The subject is 18–29, female. No relevant systemic symptoms. The leg and arm are involved. Texture is reported as raised or bumpy. FST III; lay graders estimated 2 on the MST. This image was taken at an angle — 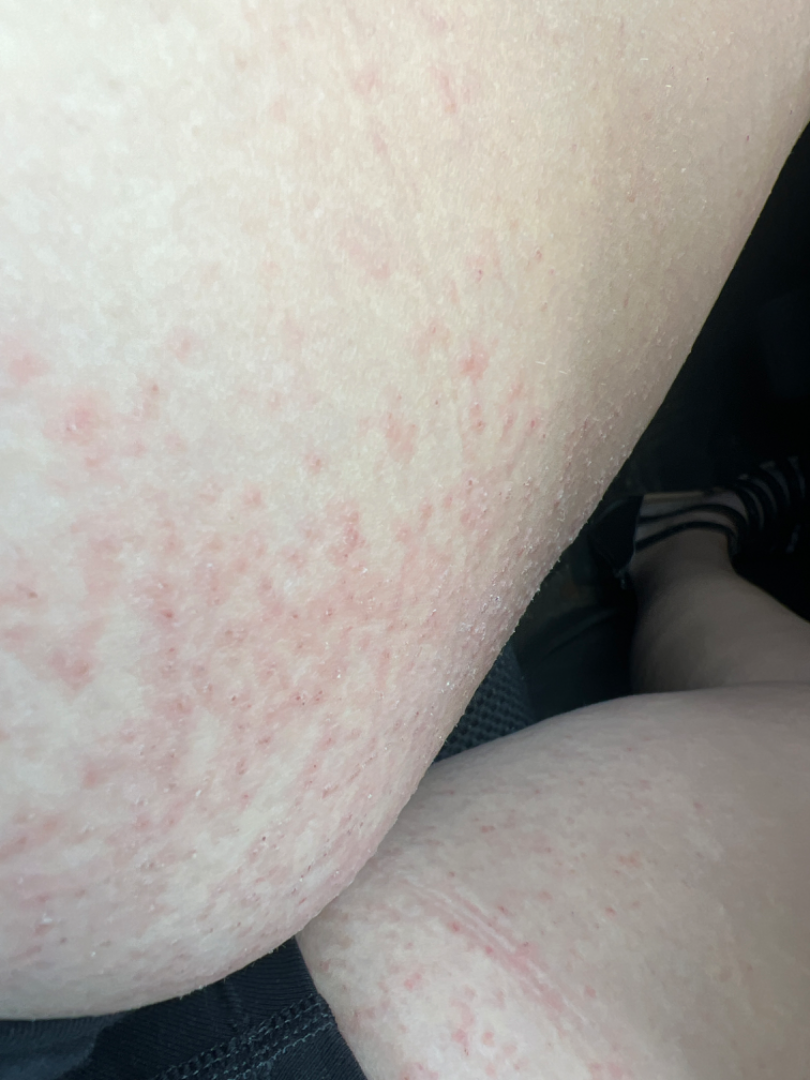Impression: On remote dermatologist review: Miliaria and Acute generalised exanthematous pustulosis were each considered, in no particular order.